Texture is reported as raised or bumpy · this is a close-up image · present for less than one week · the affected area is the leg · the patient described the issue as a rash · the patient reported no systemic symptoms:
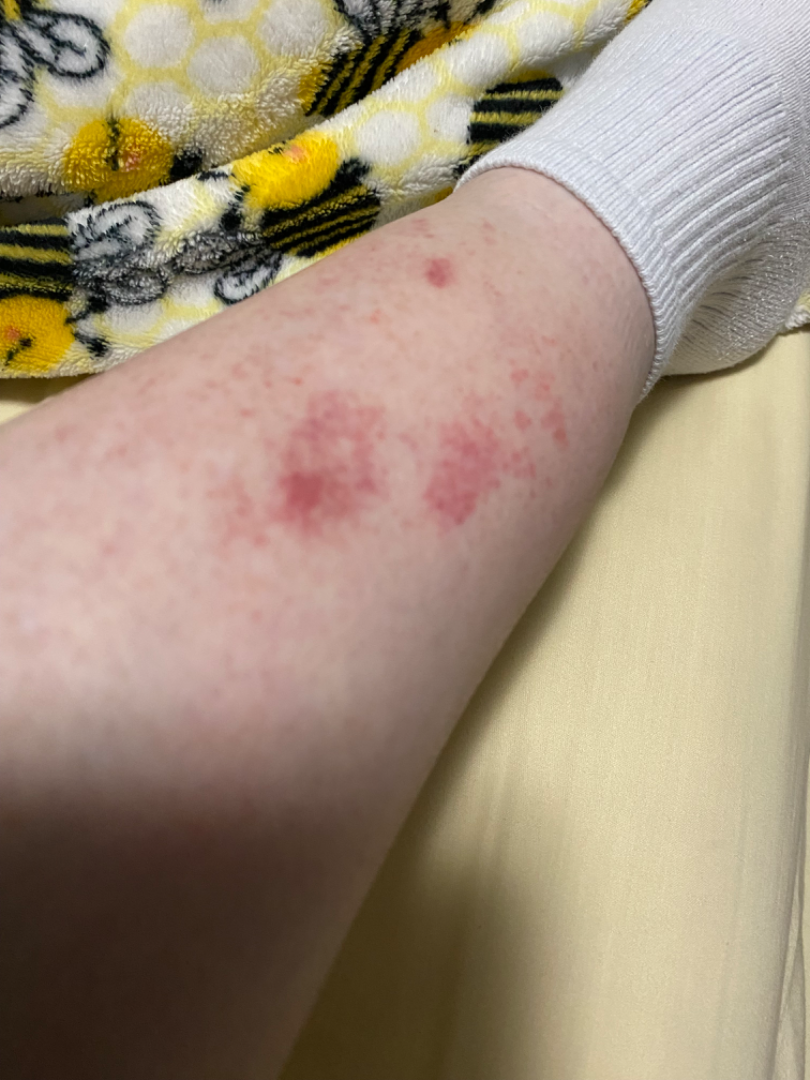Impression: Most consistent with Eczema.